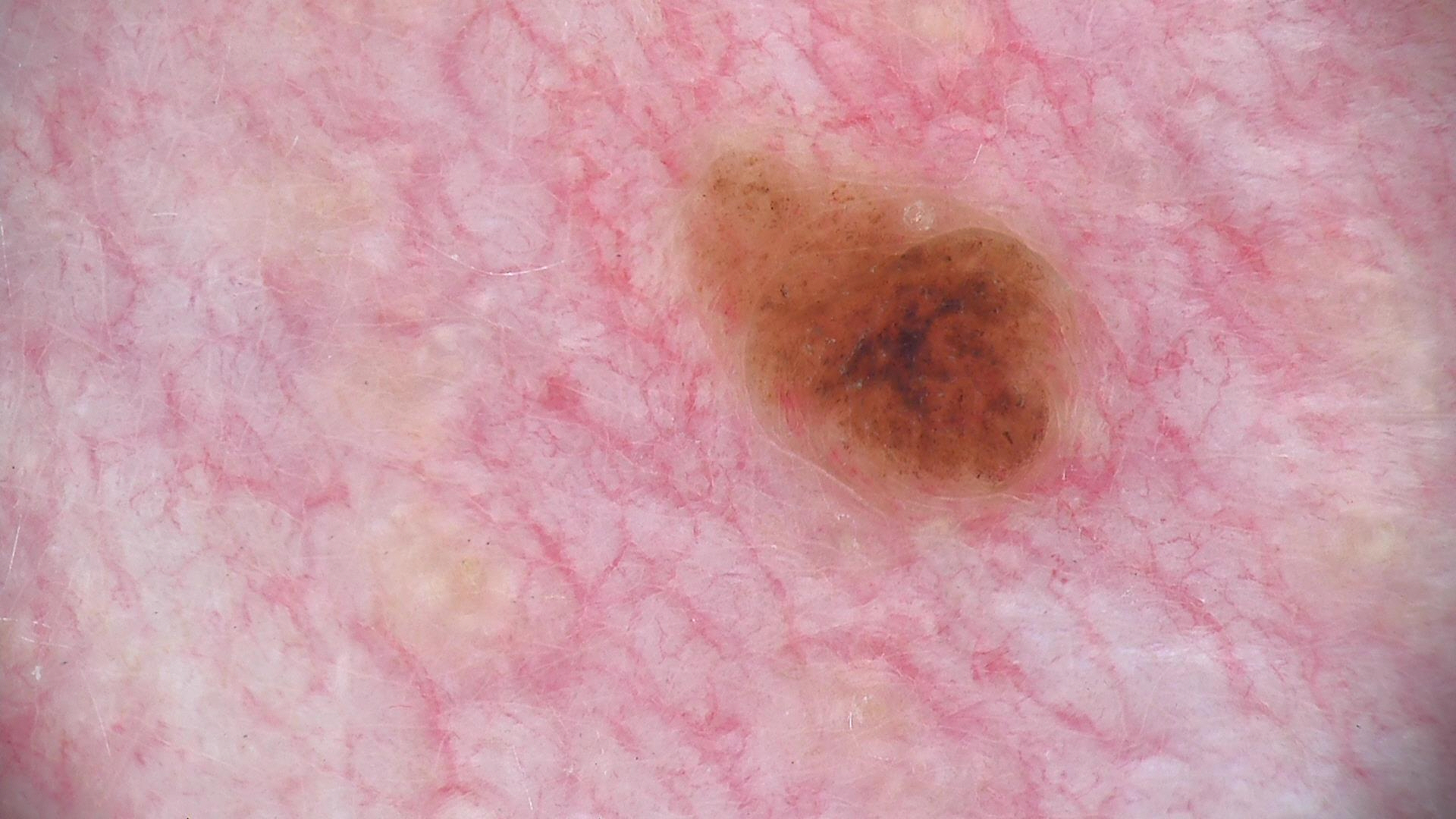The diagnostic label was a compound nevus.